A skin lesion imaged with a dermatoscope. Few moles overall by the patient's own estimate. By self-report, a personal history of cancer, a personal history of skin cancer, and no immunosuppression. Acquired for a research image collection, with no referral diagnosis. A female subject 60 years old.
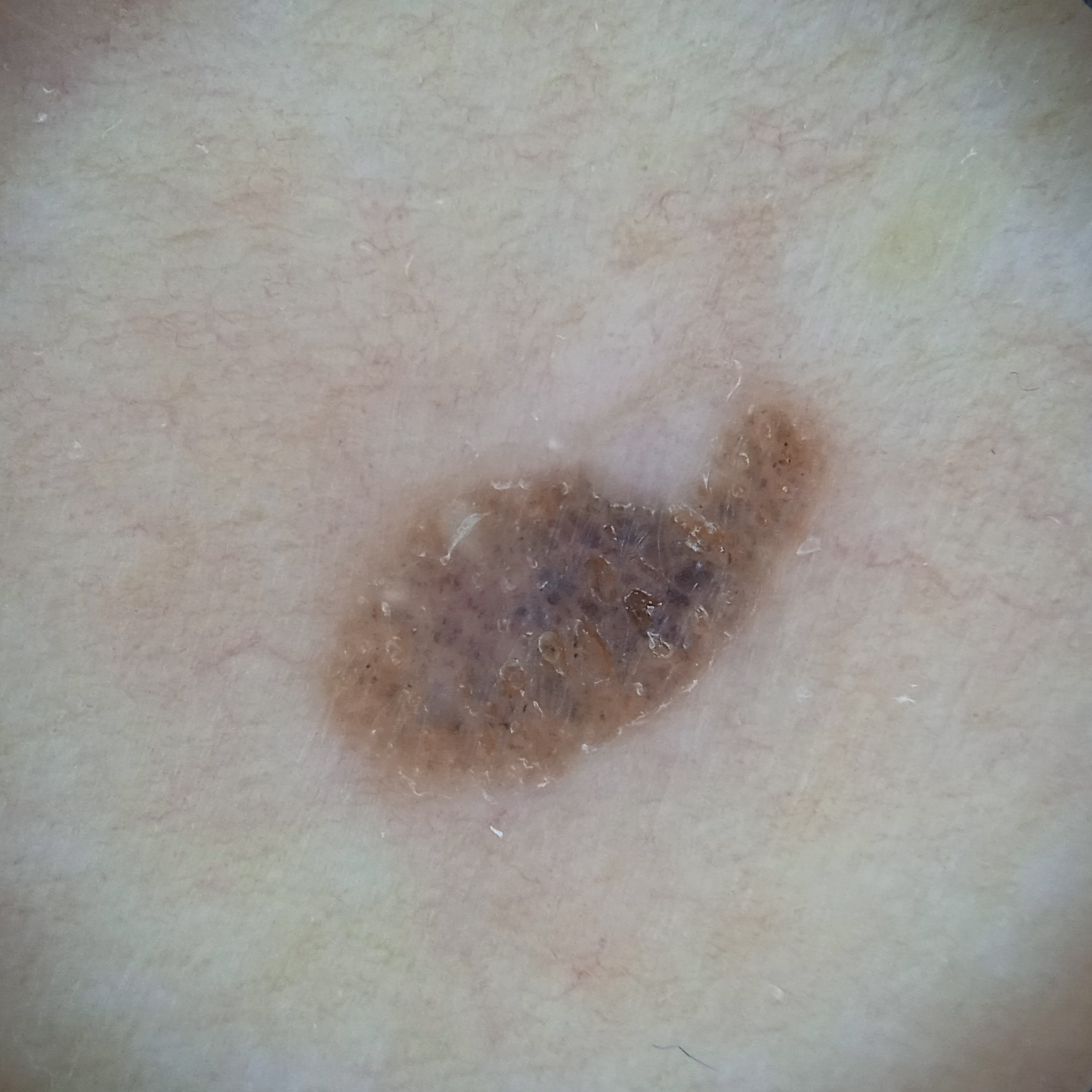The lesion is located on the torso. Reviewed by four dermatologists, the consensus diagnosis was a seborrheic keratosis; diagnostic confidence was moderate; the differential also included a melanocytic nevus.